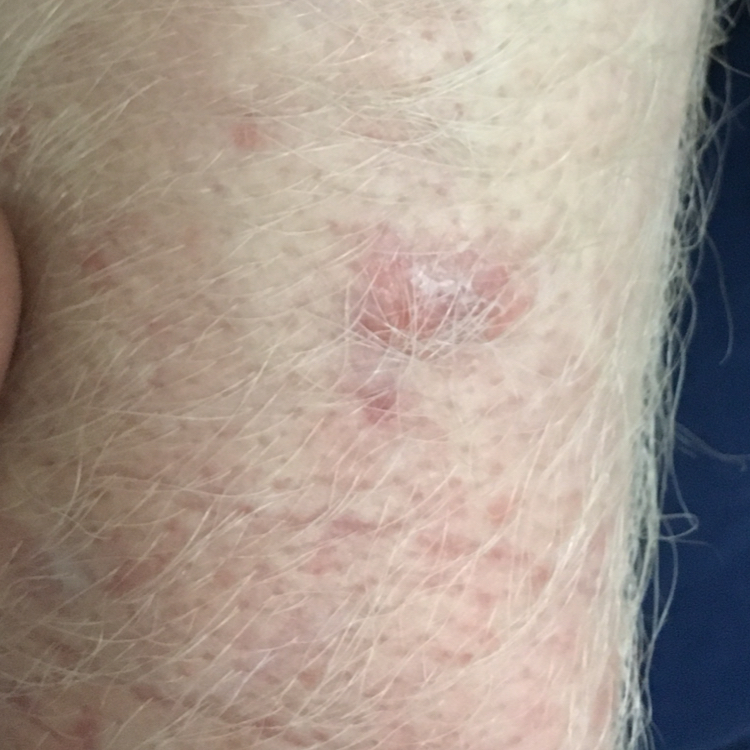Case summary:
A male patient in their 40s. A smartphone photograph of a skin lesion. The patient is FST II. By history, prior skin cancer (patient or family) and alcohol use. The lesion was found on a forearm. The lesion is roughly 7 by 3 mm. Per patient report, the lesion hurts and has grown.
Conclusion:
The clinical impression was an actinic keratosis.